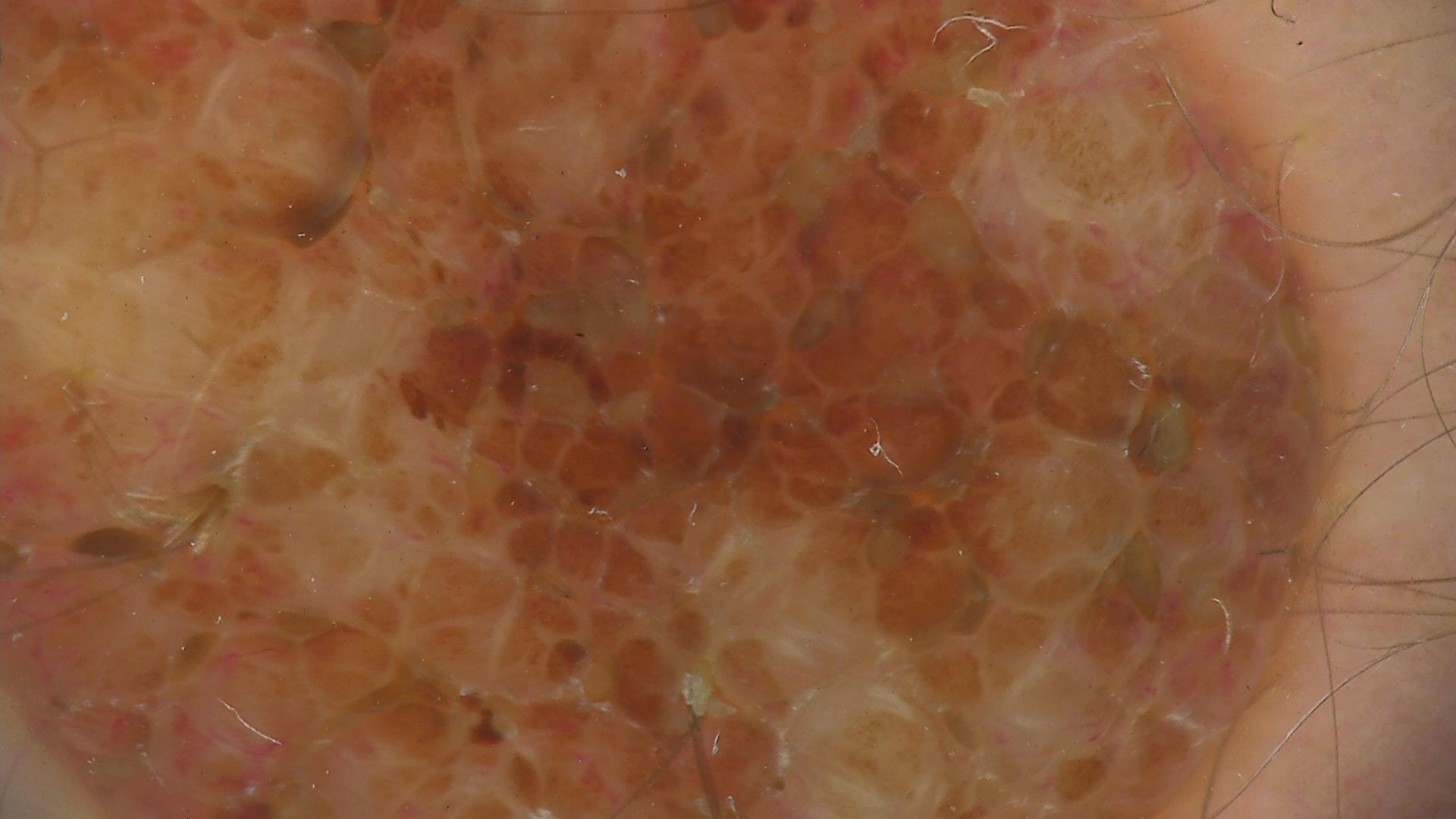A skin lesion imaged with a dermatoscope. The morphology is that of a banal lesion. Diagnosed as a dermal nevus.